The photograph was taken at a distance. The contributor notes burning. Skin tone: Fitzpatrick skin type III; non-clinician graders estimated MST 2 or 3 (two reviewer pools). The contributor notes the condition has been present for less than one week. The lesion involves the leg.
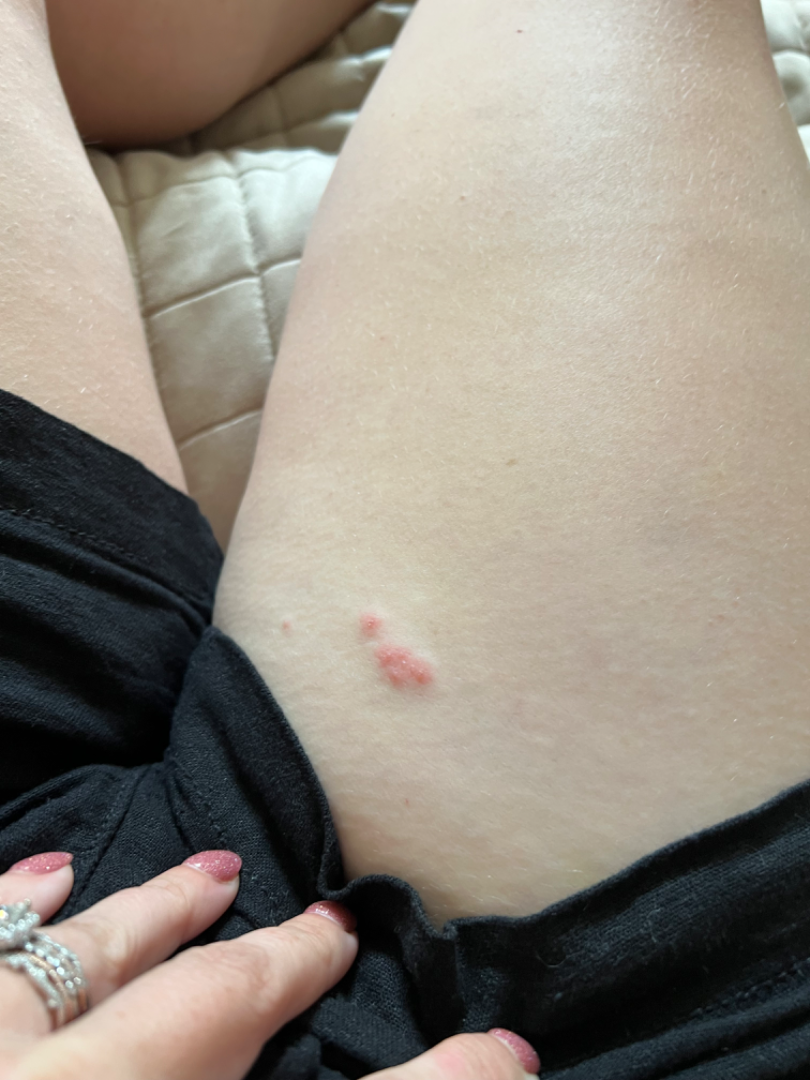Single-reviewer assessment: most consistent with Herpes Simplex.